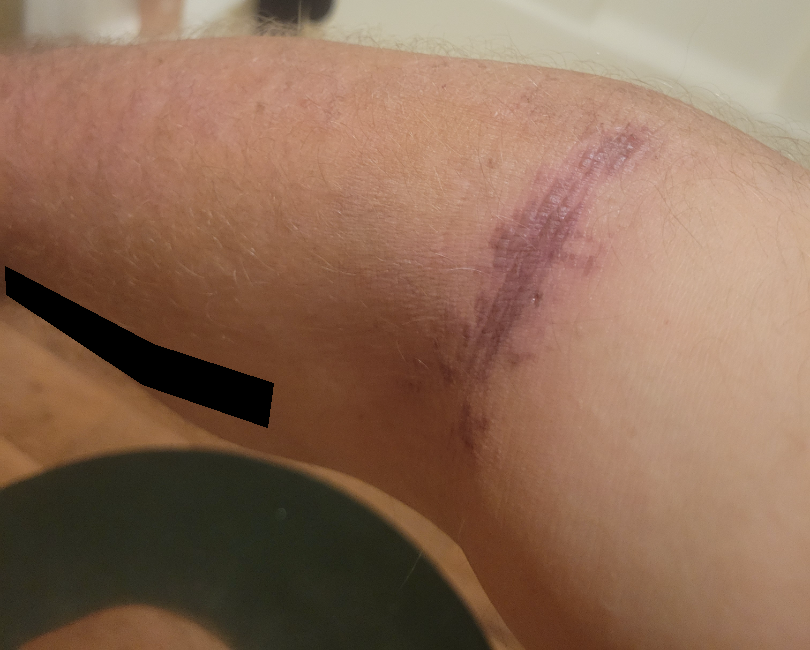skin tone = Fitzpatrick skin type II; human graders estimated 3 on the Monk skin tone scale | view = close-up | dermatologist impression = in keeping with ecchymoses.